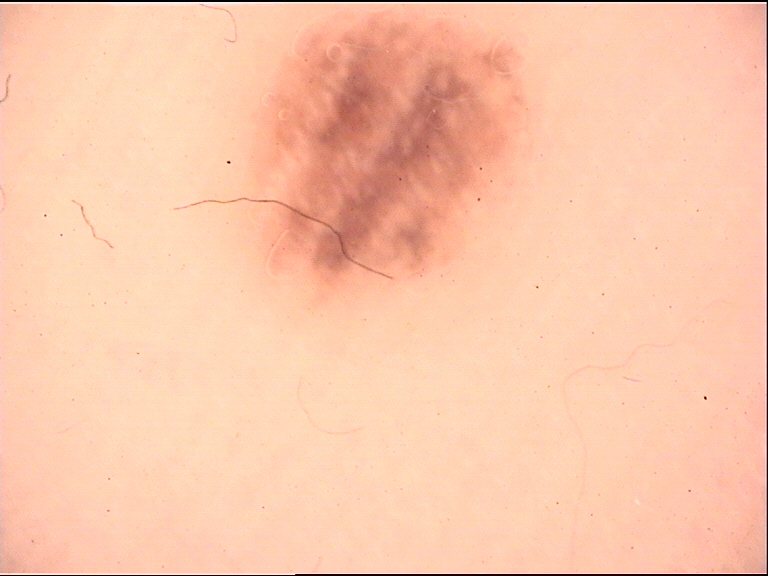Dermoscopy of a skin lesion.
The diagnostic label was a banal lesion — an acral junctional nevus.